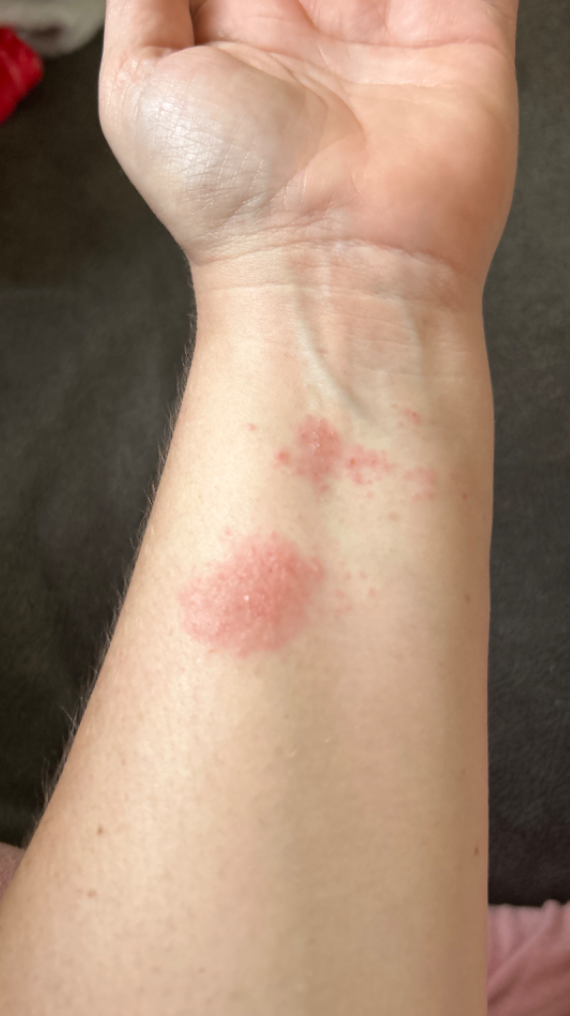Patient information: The photograph is a close-up of the affected area. The subject is a female aged 40–49. The lesion involves the arm. Review: On teledermatology review, Allergic Contact Dermatitis (weight 1.00).